The photo was captured at a distance. The lesion involves the head or neck — 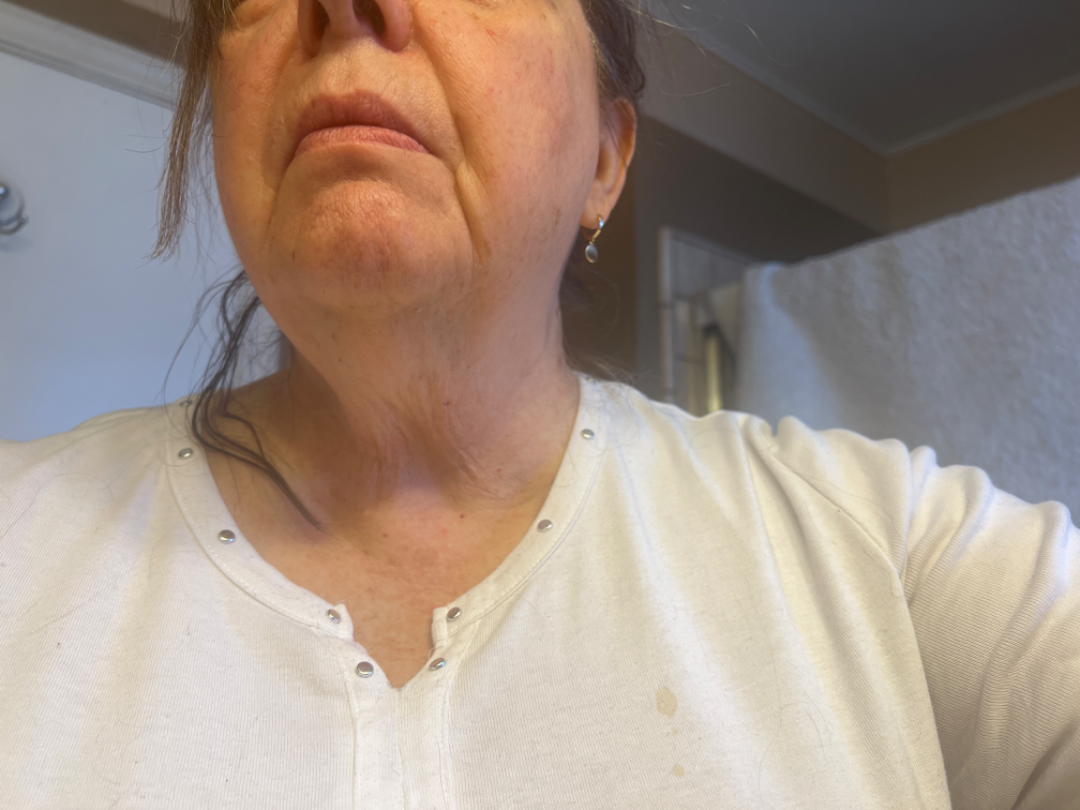The dermatologist could not determine a likely condition from the photograph alone. Present for three to twelve months.